Dermoscopy of a skin lesion: 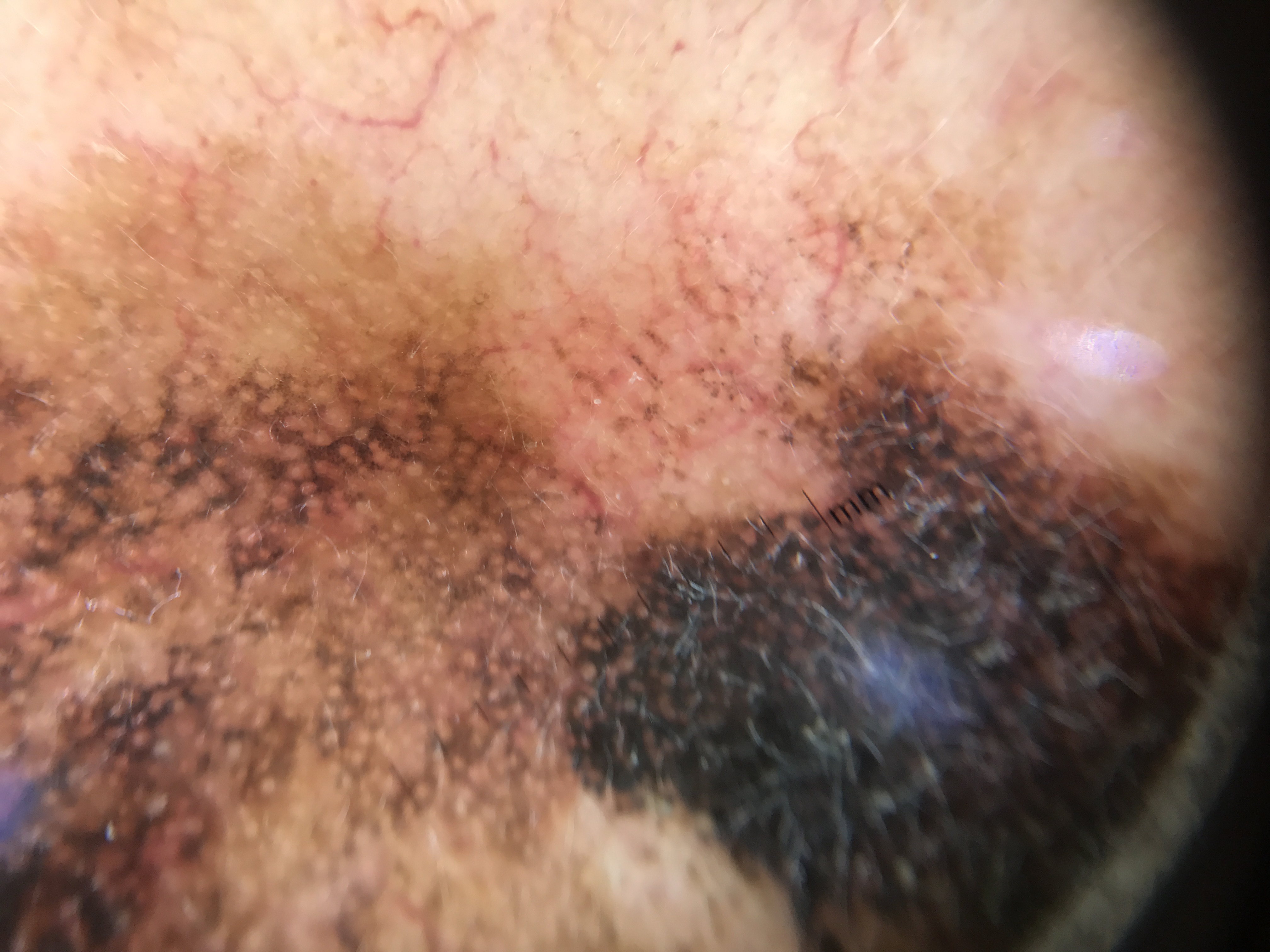The biopsy diagnosis was a lentigo maligna.